A dermoscopic close-up of a skin lesion.
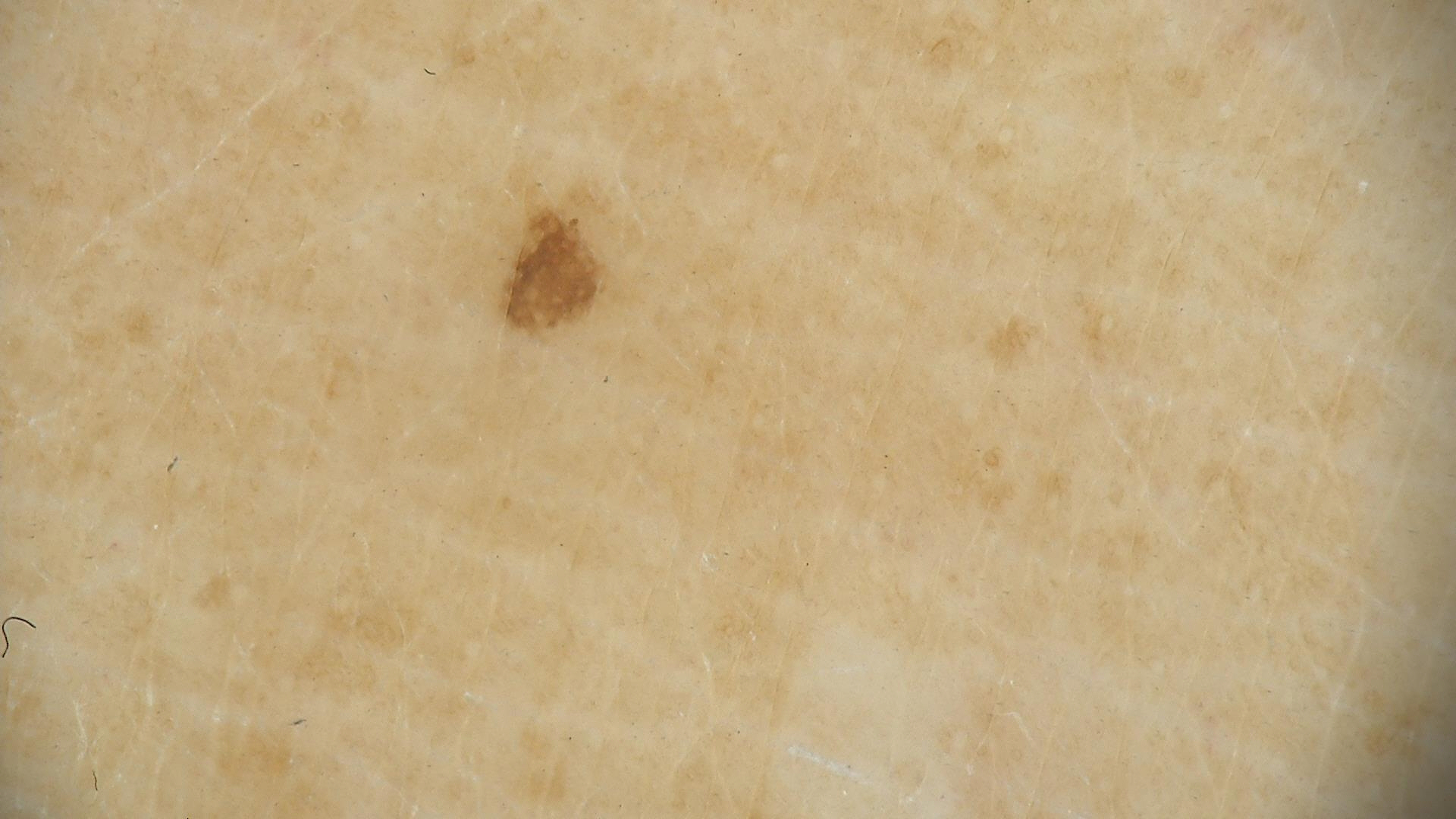<lesion>
<lesion_type>
<main_class>keratinocytic</main_class>
</lesion_type>
<diagnosis>
<name>seborrheic keratosis</name>
<code>sk</code>
<malignancy>benign</malignancy>
<super_class>non-melanocytic</super_class>
<confirmation>expert consensus</confirmation>
</diagnosis>
</lesion>